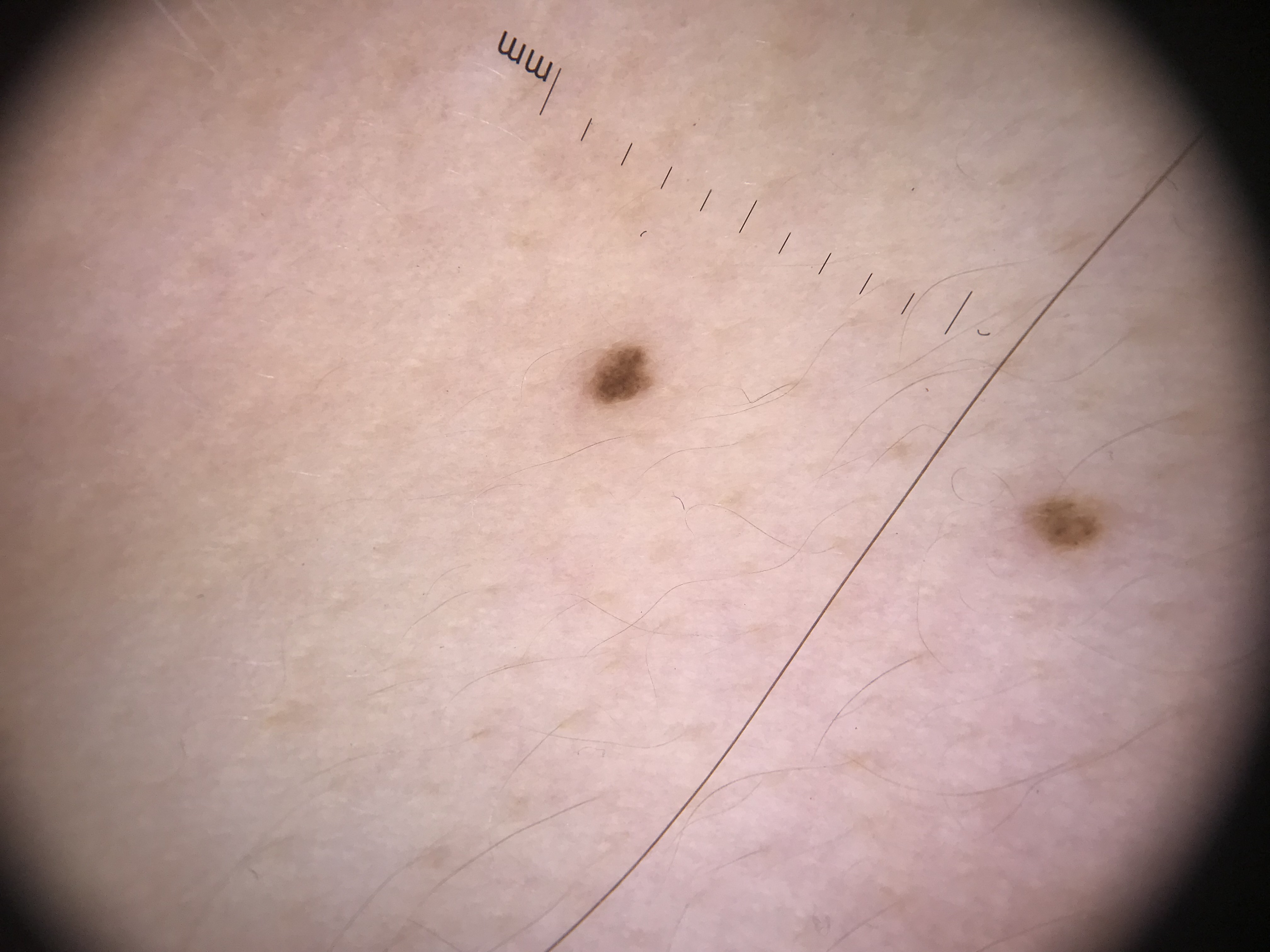Classified as a junctional nevus.